Acquired for a research image collection, with no referral diagnosis · the patient says their skin reddens with sun exposure · a female patient age 15 · few moles overall by the patient's own estimate · a dermoscopic image of a skin lesion.
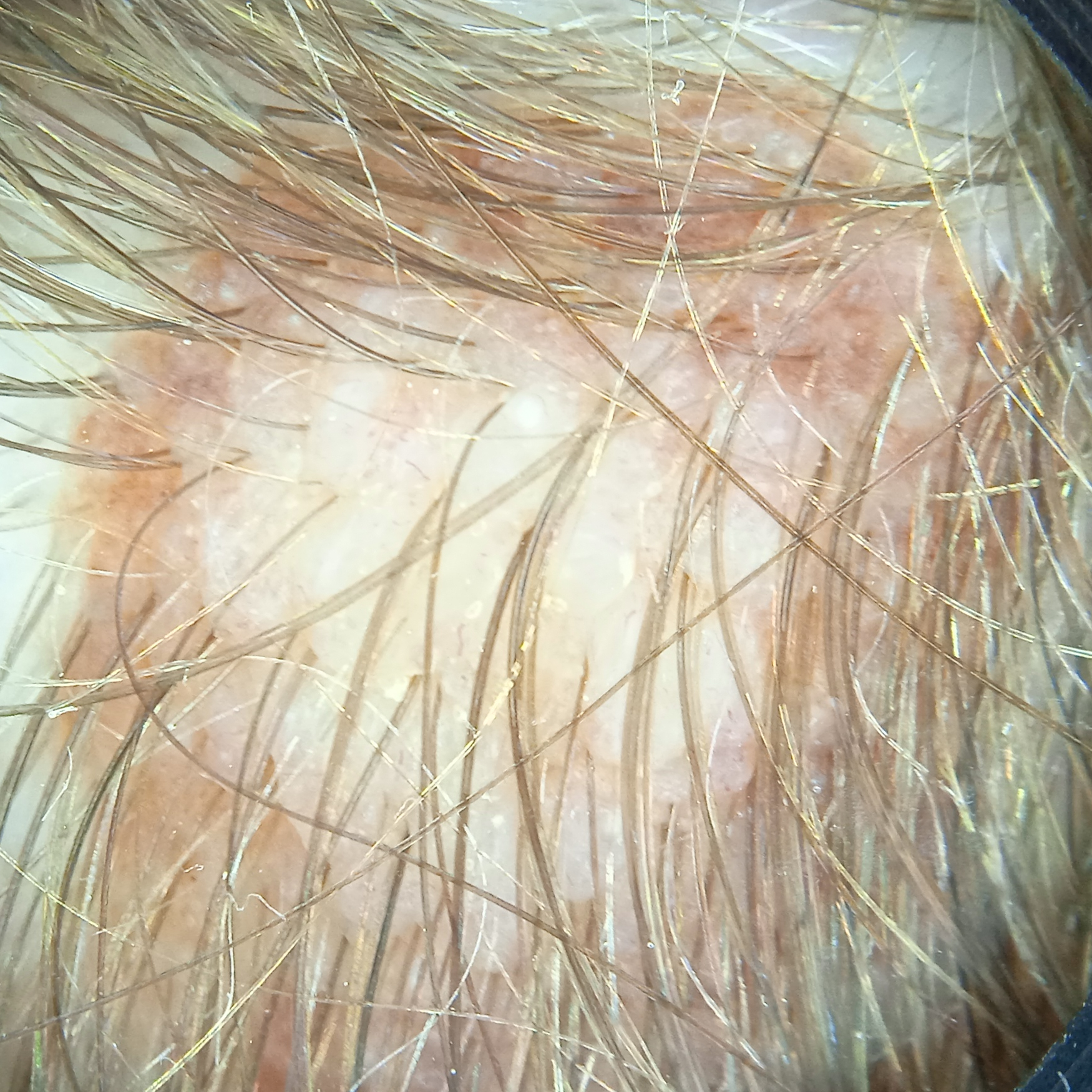anatomic site=the head; size=9.1 mm; diagnostic label=melanocytic nevus (dermatologist consensus).